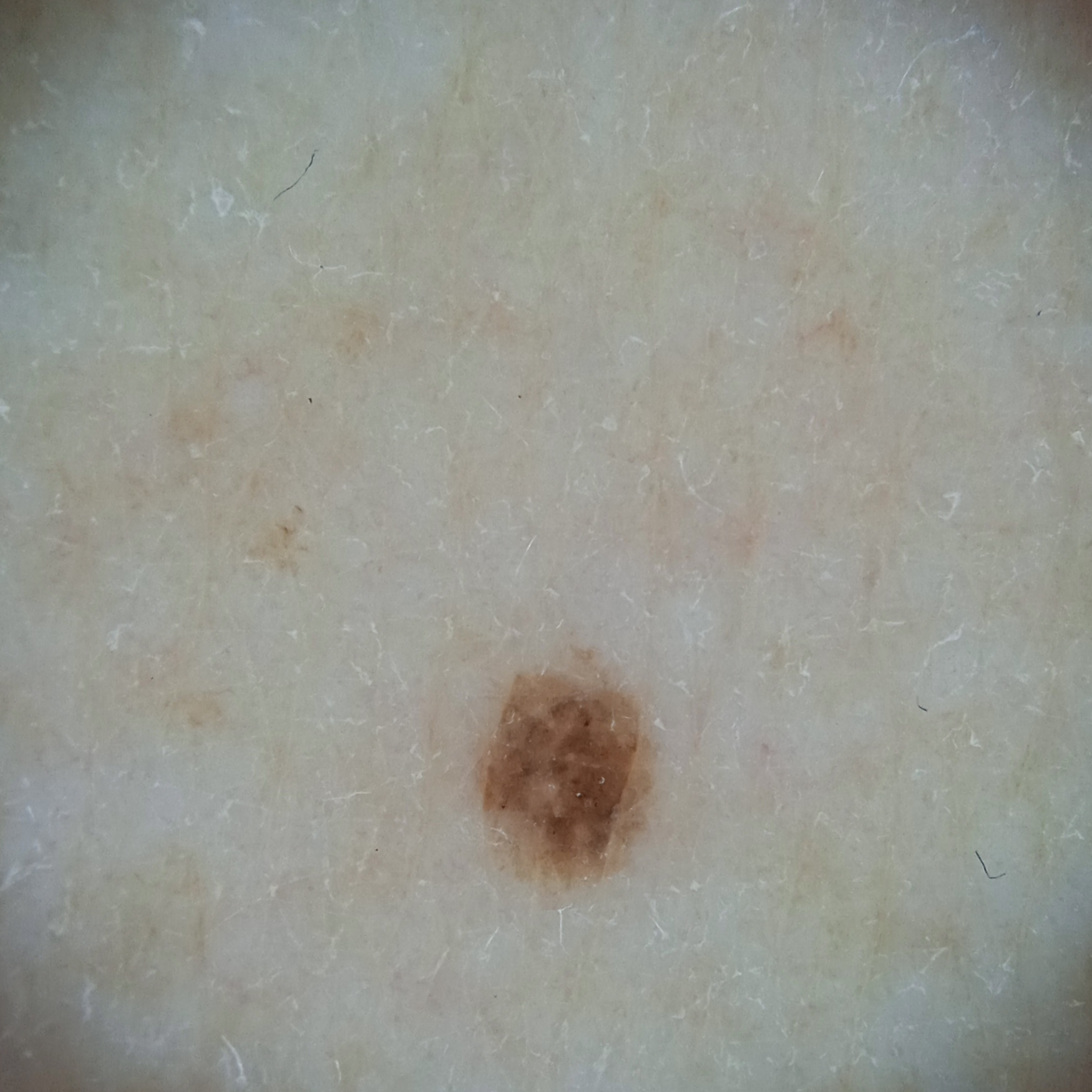nevus count: a moderate number of melanocytic nevi | subject: female, 50 years of age | clinical context: research study (no referral diagnosis) | relevant history: a personal history of skin cancer, no family history of skin cancer | lesion size: 2.5 mm | assessment: melanocytic nevus (dermatologist consensus).